The patient is skin type II.
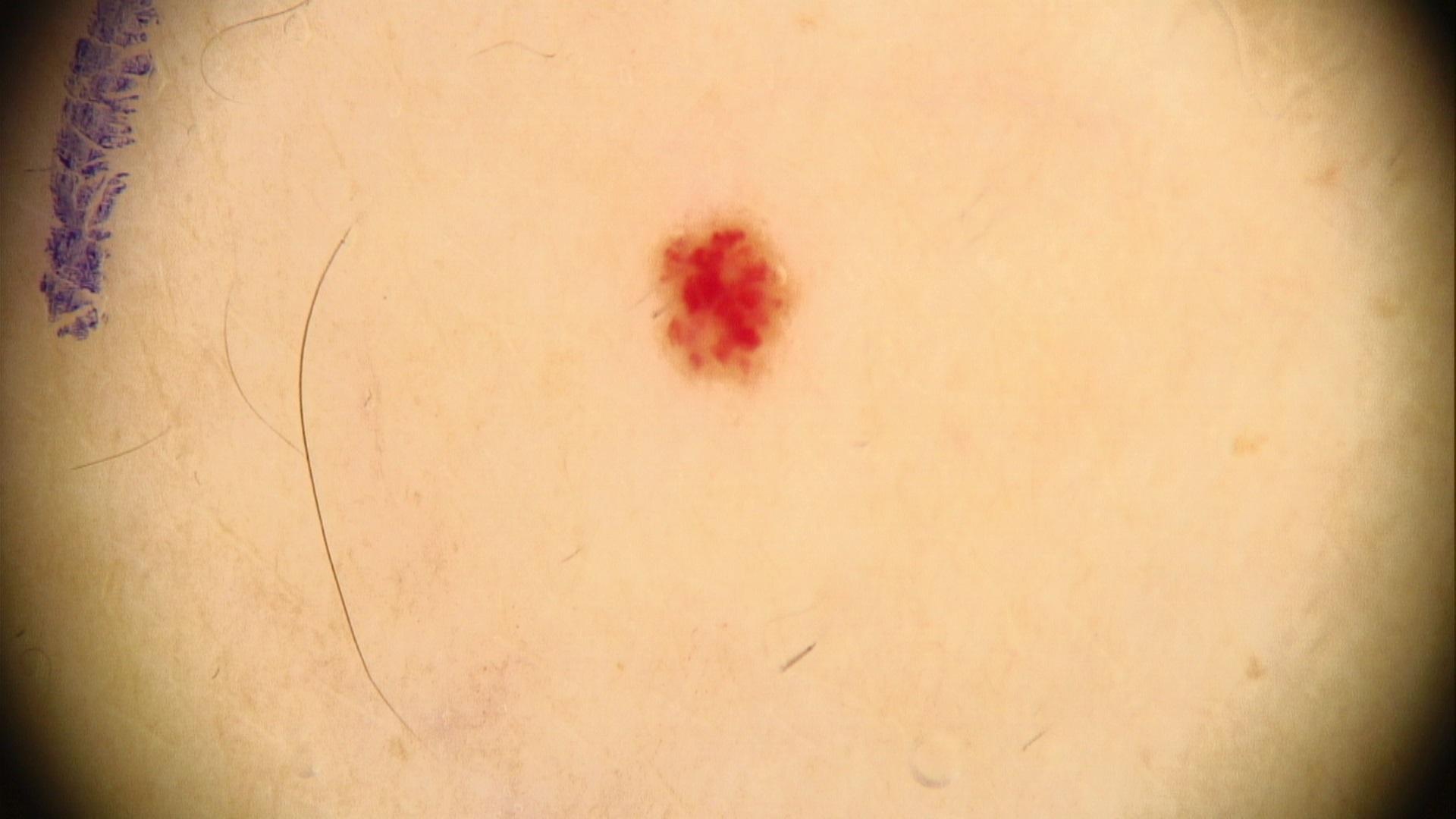location — a lower extremity | impression — vascular lesion.